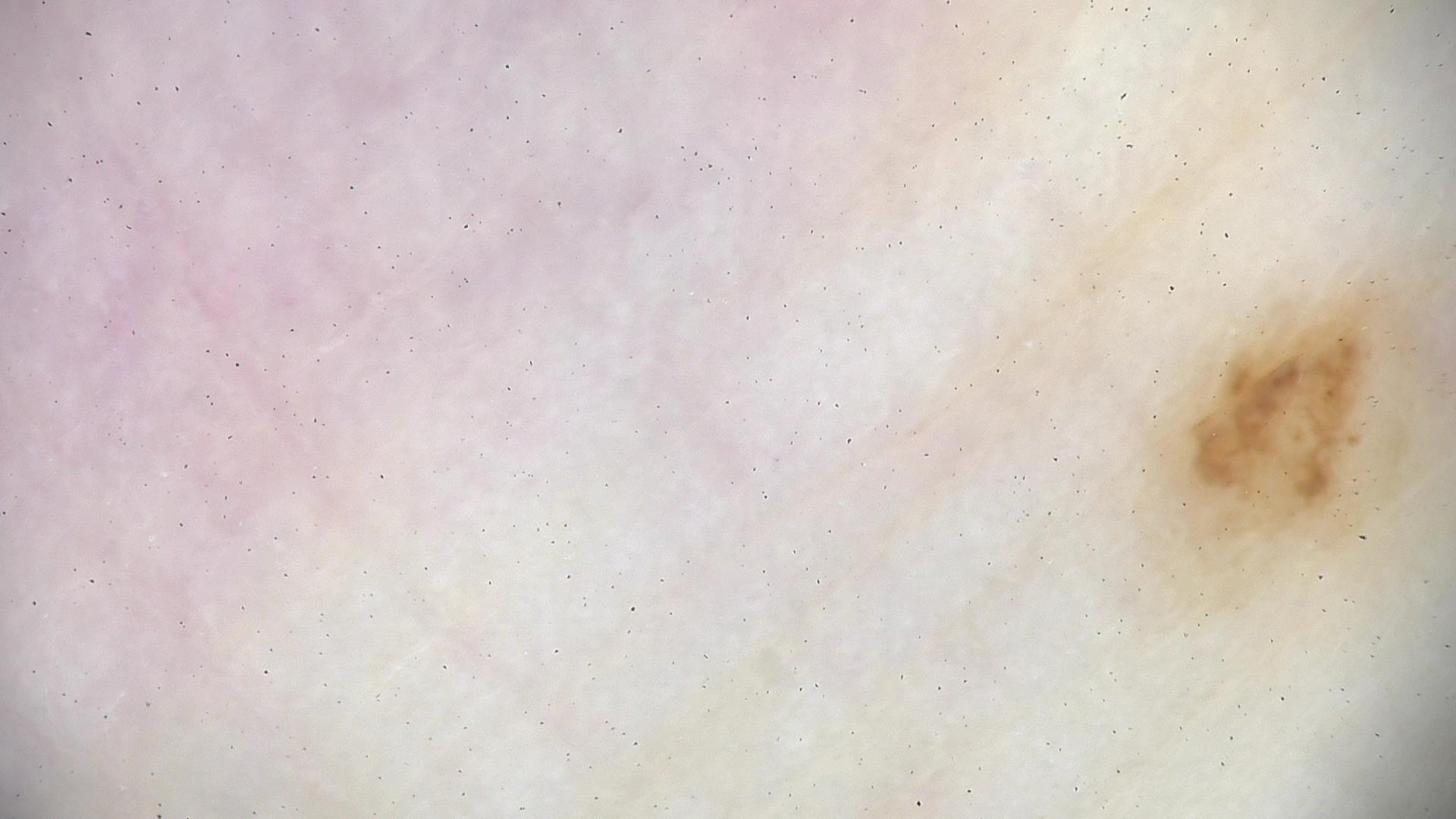Dermoscopy of a skin lesion. Consistent with a benign lesion — an acral dysplastic junctional nevus.